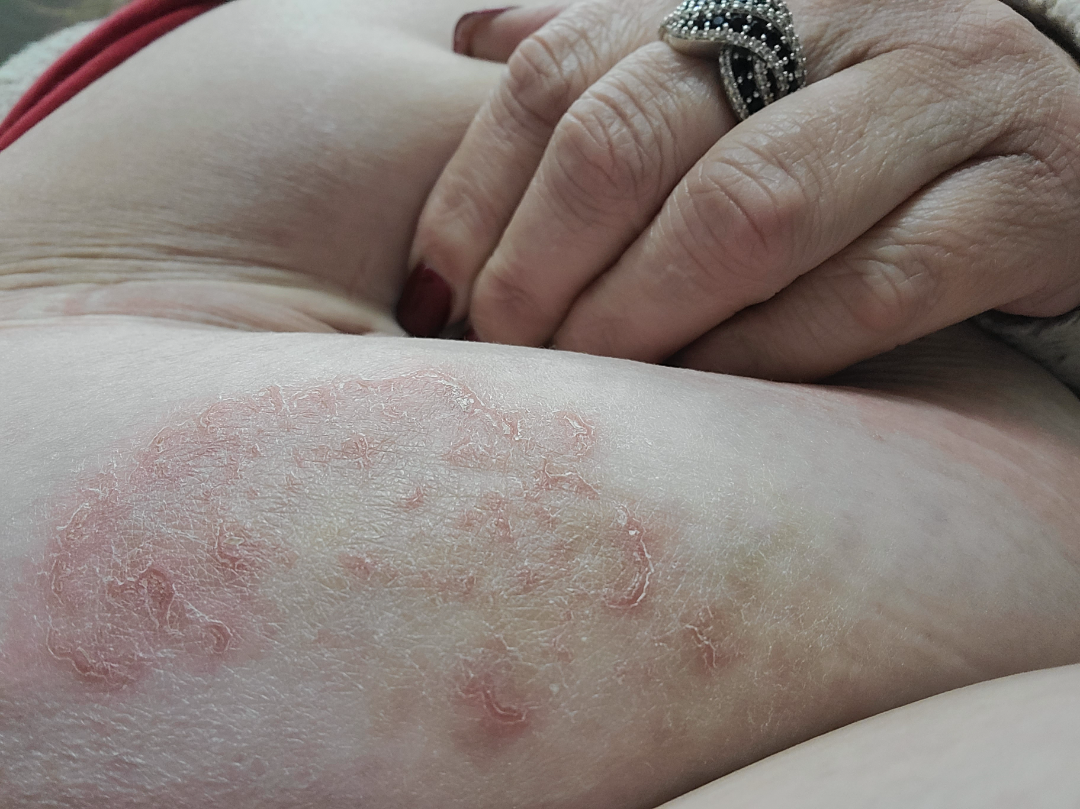On dermatologist assessment of the image, Eczema and Acute and chronic dermatitis were considered with similar weight.